Skin tone: Fitzpatrick II; human graders estimated Monk Skin Tone 2 or 3 (two reviewer pools), the photo was captured at a distance — 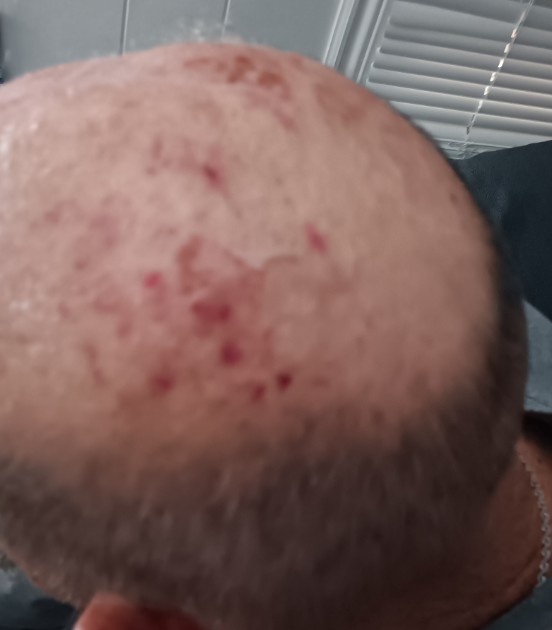Q: What was the assessment?
A: unable to determine